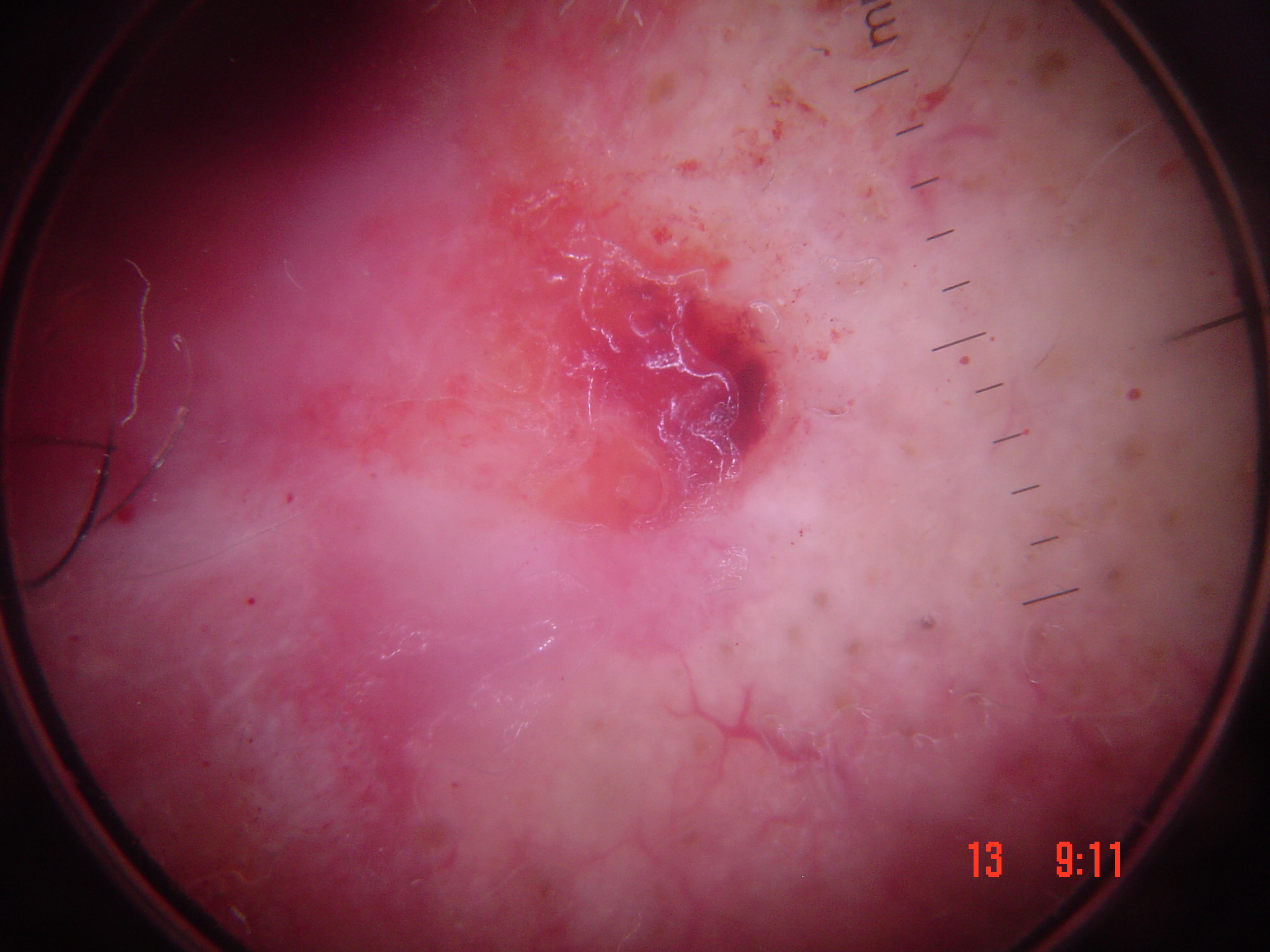Case:
- image type · dermatoscopy
- pathology · squamous cell carcinoma (biopsy-proven)